A dermoscopic close-up of a skin lesion.
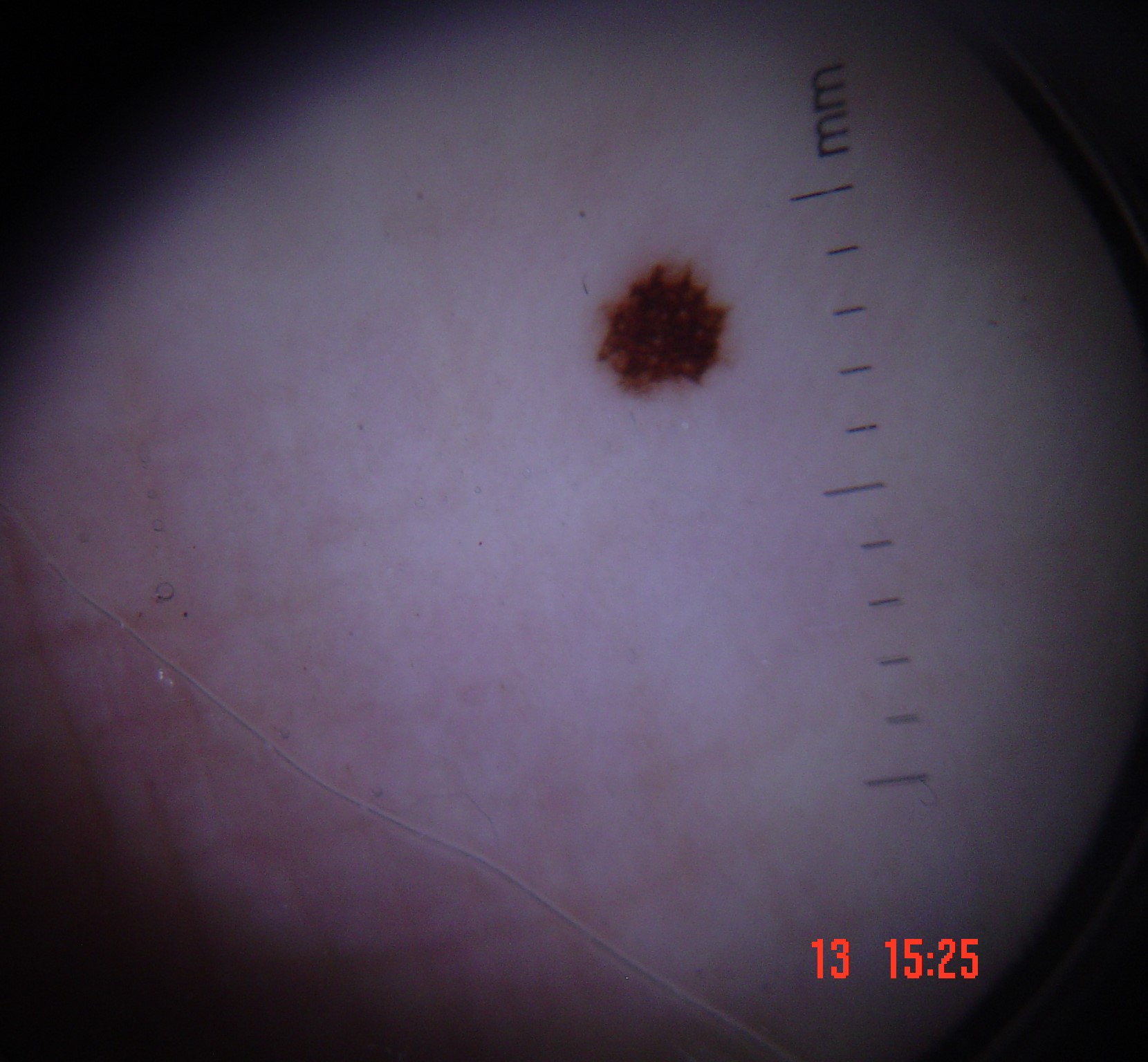The diagnostic label was an acral dysplastic junctional nevus.